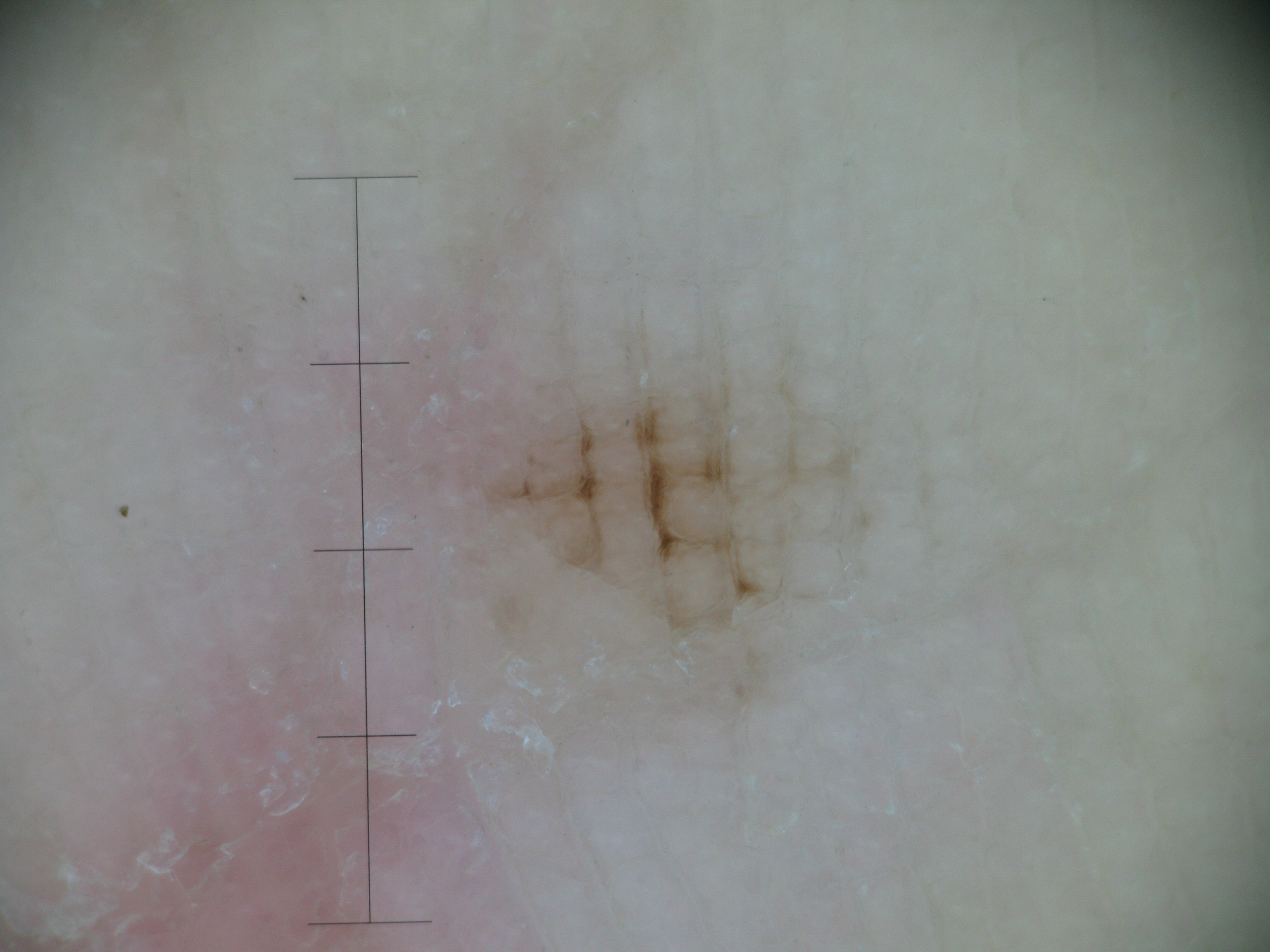<lesion>
  <image>dermatoscopy</image>
  <diagnosis>
    <name>acral junctional nevus</name>
    <code>ajb</code>
    <malignancy>benign</malignancy>
    <super_class>melanocytic</super_class>
    <confirmation>expert consensus</confirmation>
  </diagnosis>
</lesion>